A skin lesion imaged with a dermatoscope. The patient was assessed as Fitzpatrick phototype I. The chart notes a prior melanoma.
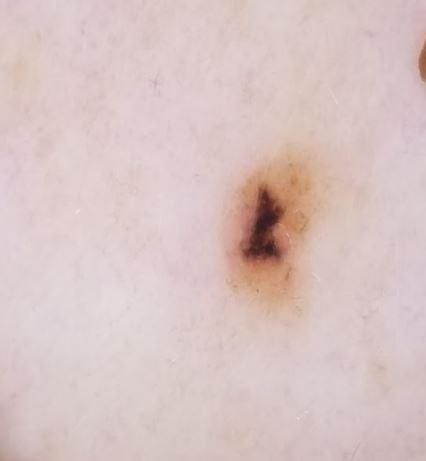anatomic site: the trunk, specifically the posterior trunk
diagnosis: Melanoma (biopsy-proven)